Fitzpatrick II. A male patient age 59. A clinical photograph of a skin lesion.
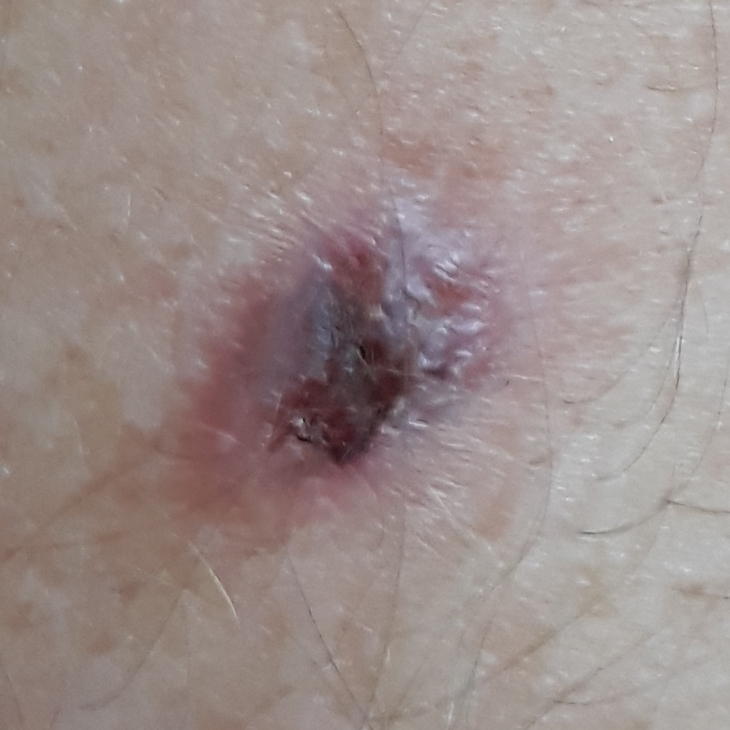The lesion was found on the back. The lesion measures approximately 7 × 5 mm. Histopathological examination showed a skin cancer — a basal cell carcinoma.